A dermatoscopic image of a skin lesion.
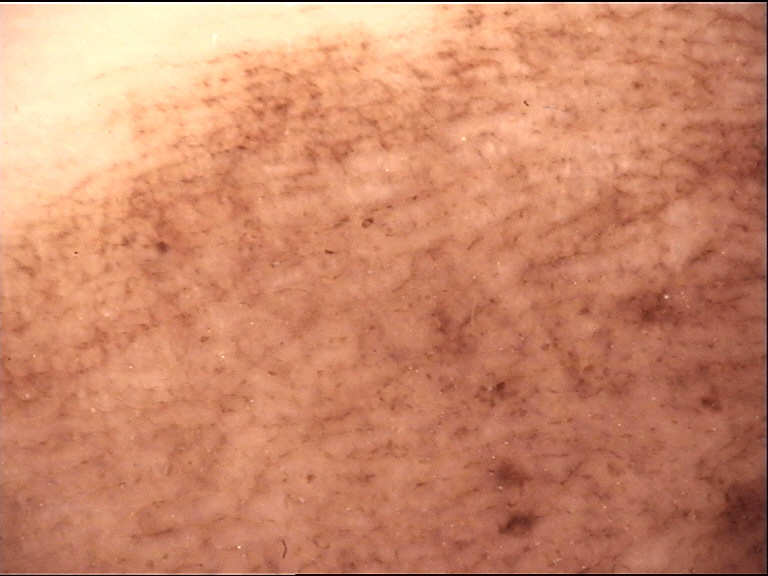Summary:
This is a banal lesion.
Impression:
The diagnosis was an acral compound nevus.